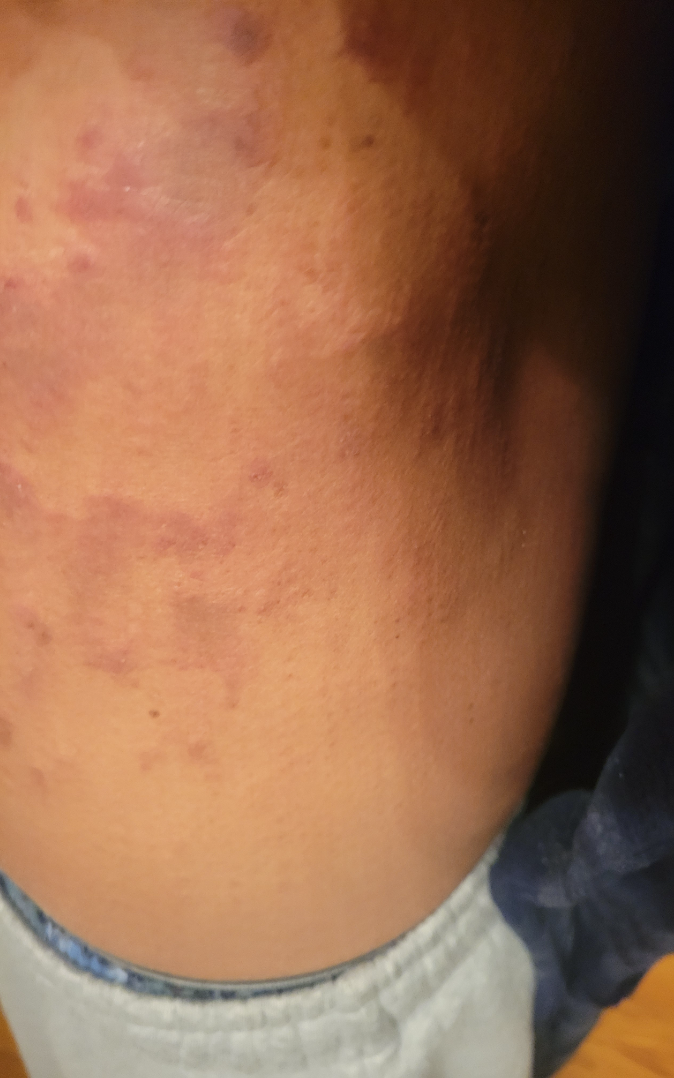assessment — could not be assessed; patient's own categorization — a rash; location — leg; history — one to four weeks; lesion symptoms — bothersome appearance; shot type — close-up; skin tone — FST IV; surface texture — flat.